The patient says their skin tans without first burning; a dermatoscopic image of a skin lesion; on a questionnaire the patient reported a family history of skin cancer, a personal history of cancer, and no immunosuppression; a female subject aged 92; referred for assessment of suspected basal cell carcinoma — 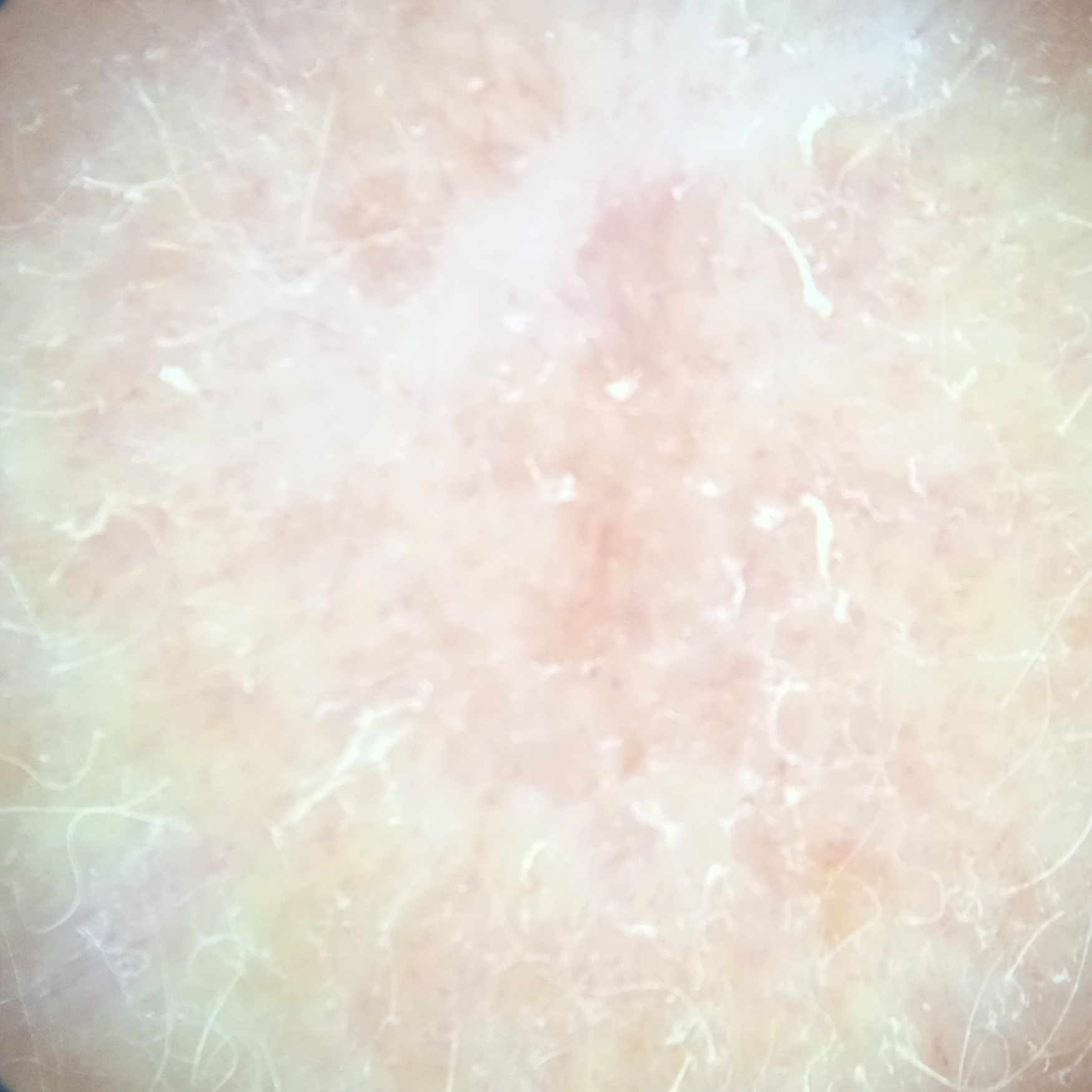{"lesion_size": {"diameter_mm": 11.5}, "diagnosis": {"name": "basal cell carcinoma", "malignancy": "malignant", "procedure": "excision", "tumor_thickness_mm": 2.6}}